The photograph is a close-up of the affected area, located on the leg and arm.
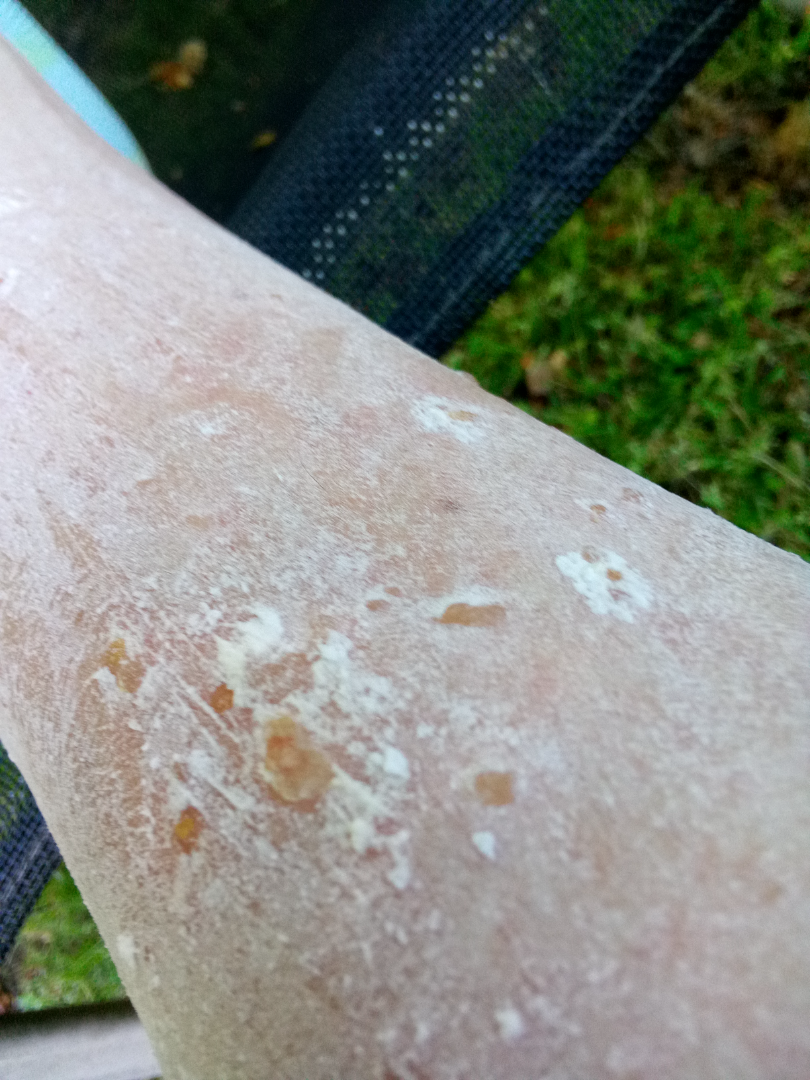Associated systemic symptoms include fatigue.
The patient considered this a rash.
The lesion is described as raised or bumpy and fluid-filled.
Reported duration is less than one week.
The reviewing dermatologist's impression was: Stasis Dermatitis (most likely).